A dermoscopy image of a single skin lesion: 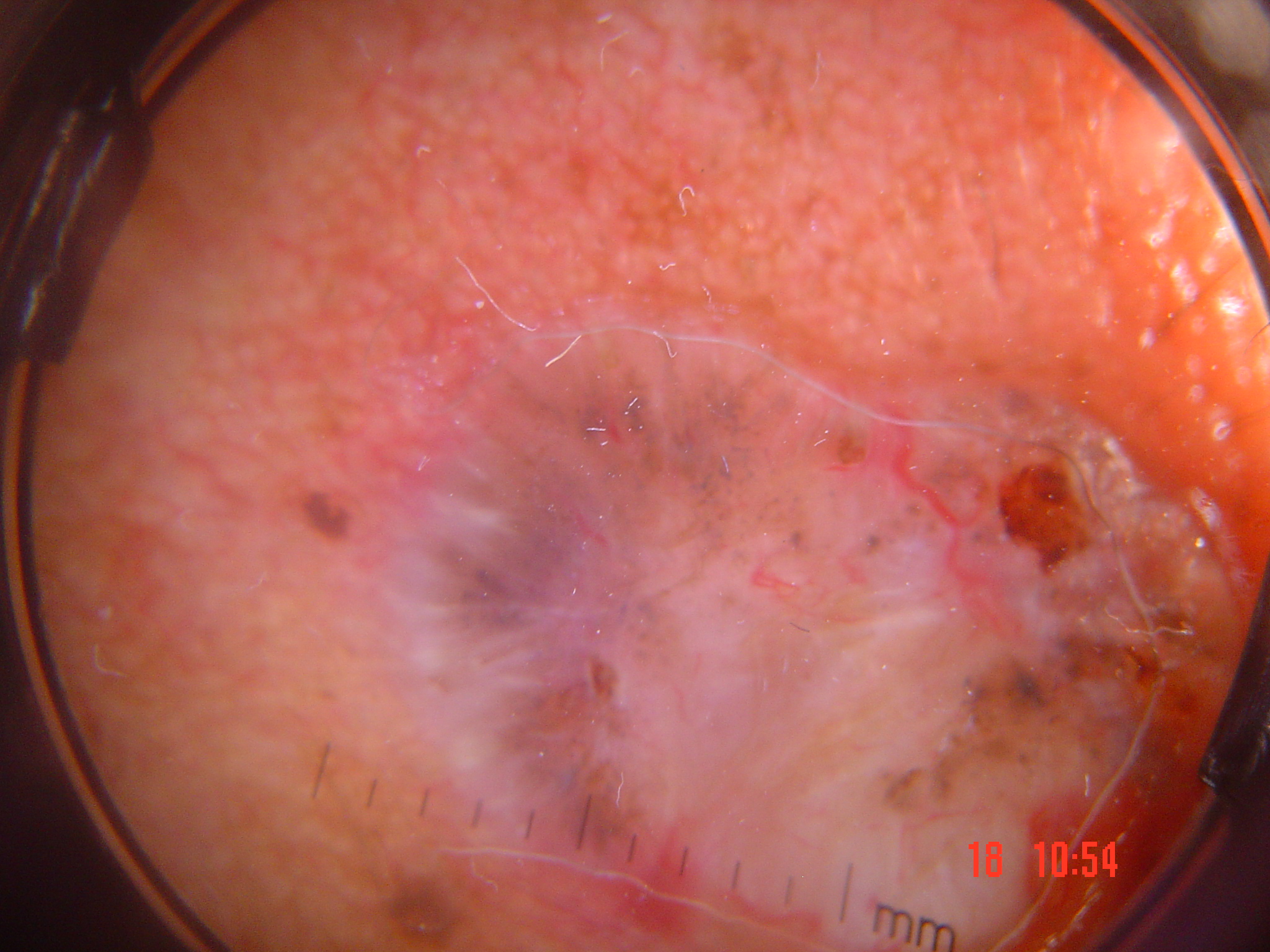Findings: The morphology is that of a keratinocytic lesion. Pathology: Biopsy-confirmed as a basal cell carcinoma.